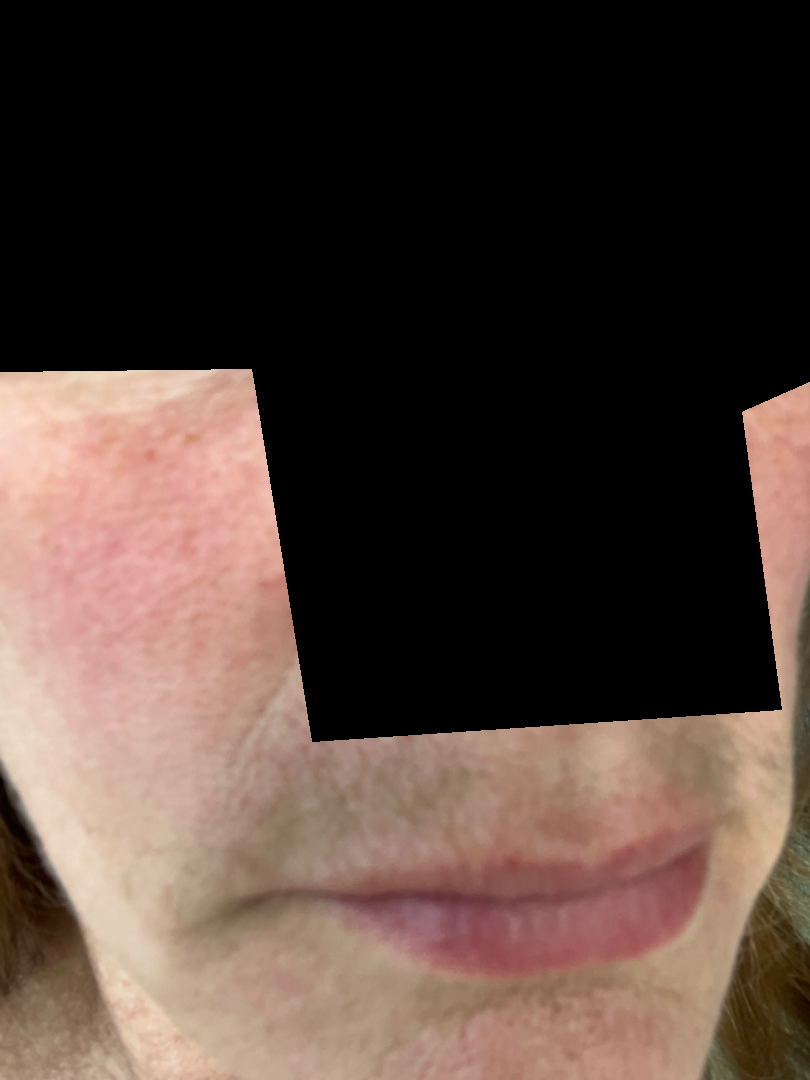Impression: Diagnostic features were not clearly distinguishable in this photograph. History: The photograph was taken at an angle.